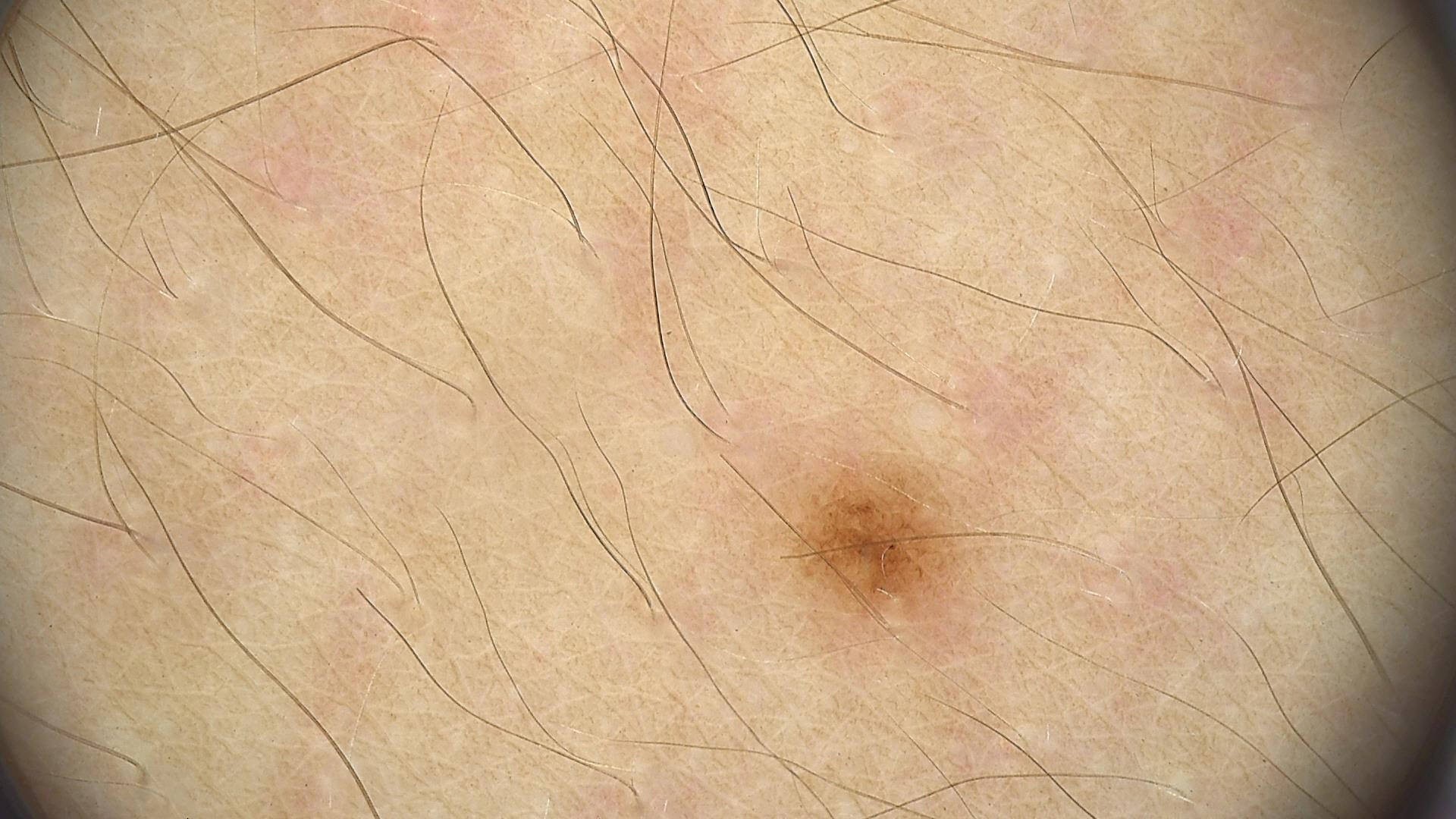image type: dermatoscopy
class: junctional nevus (expert consensus)